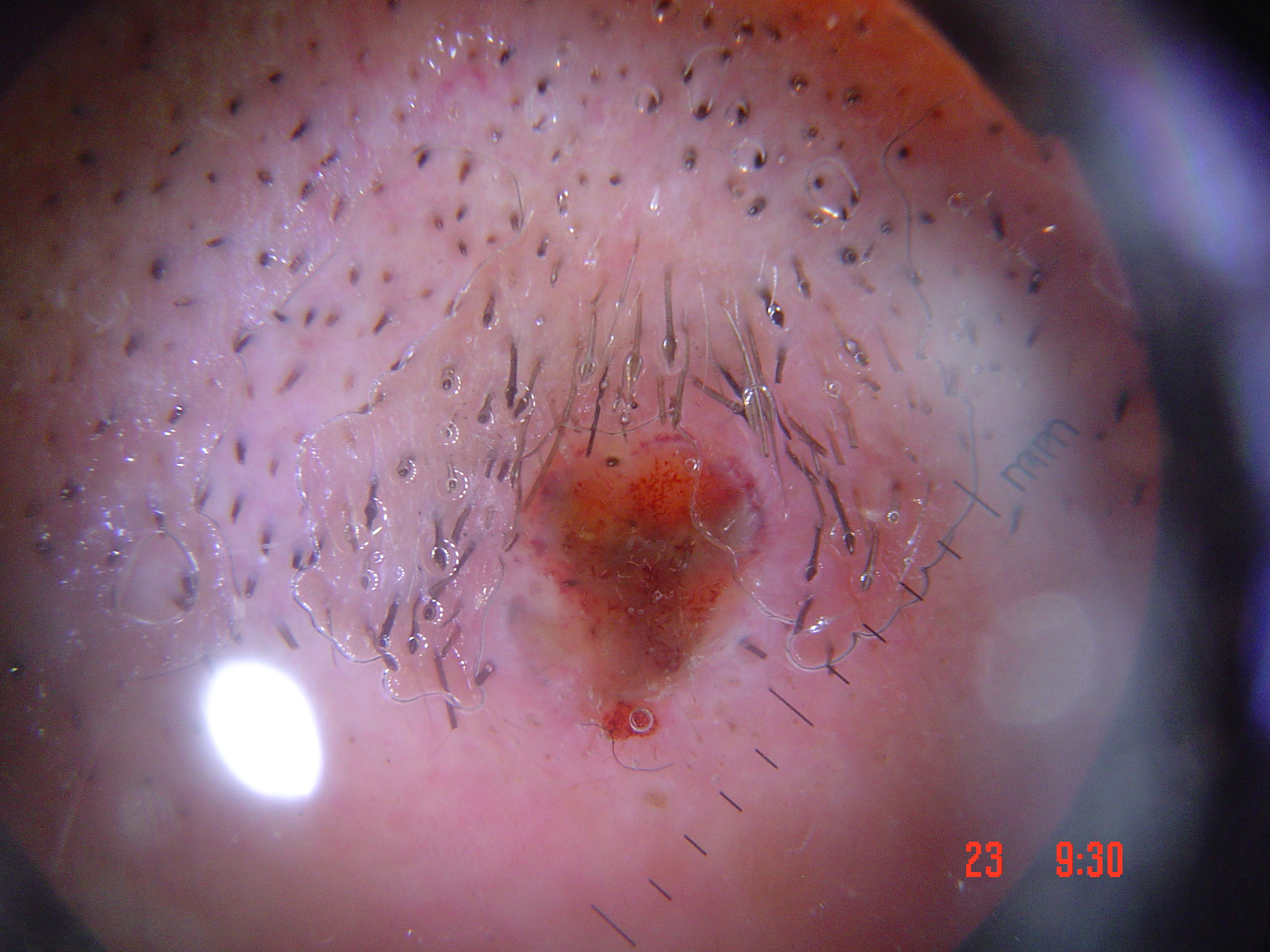diagnosis=squamous cell carcinoma (biopsy-proven).